A male patient aged 43-47, this is a dermoscopic photograph of a skin lesion — 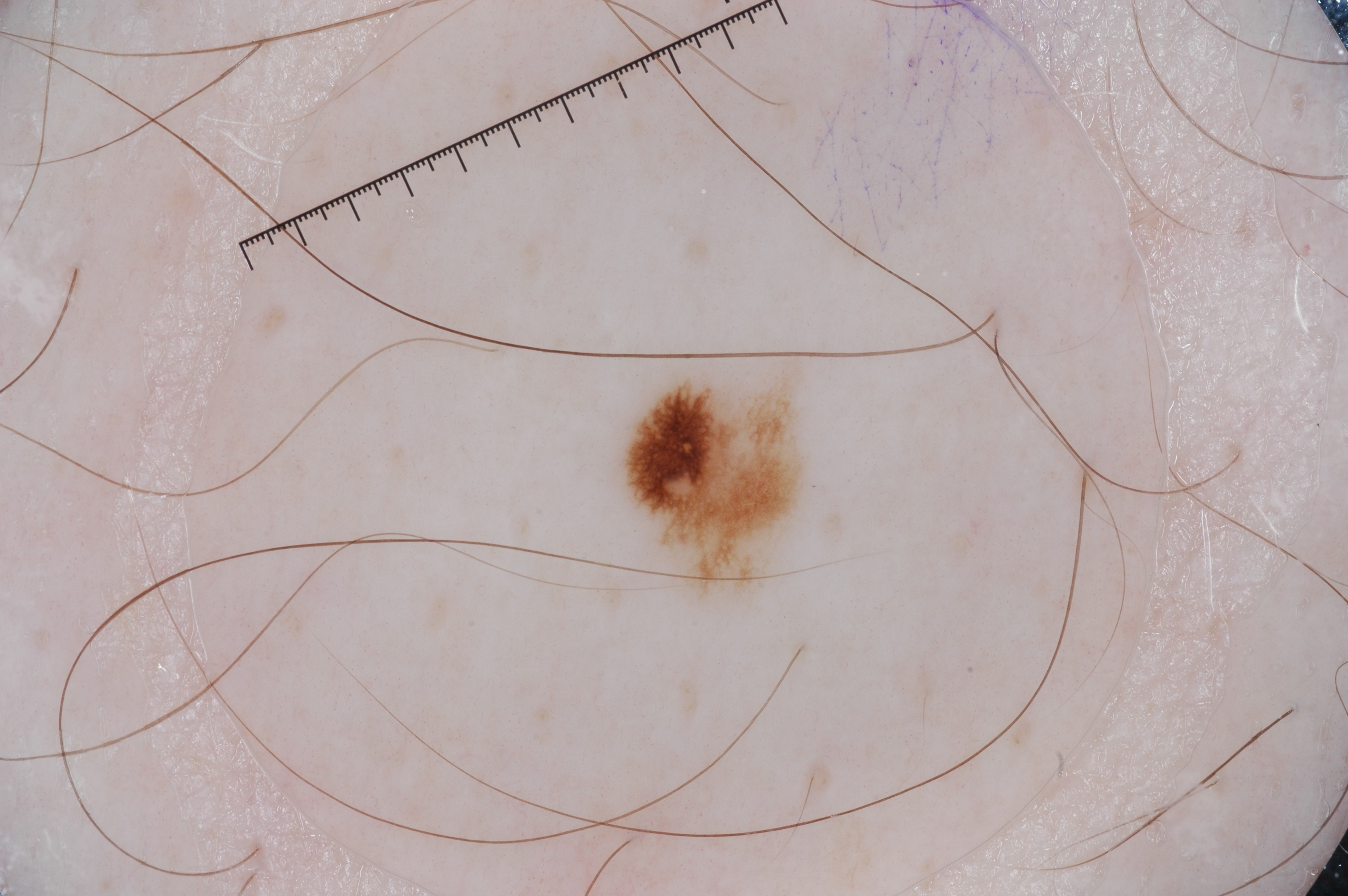lesion size — small
features — pigment network and negative network; absent: milia-like cysts and streaks
lesion location — 614/355/820/613
diagnostic label — a melanoma, a skin cancer